A skin lesion imaged with a dermatoscope.
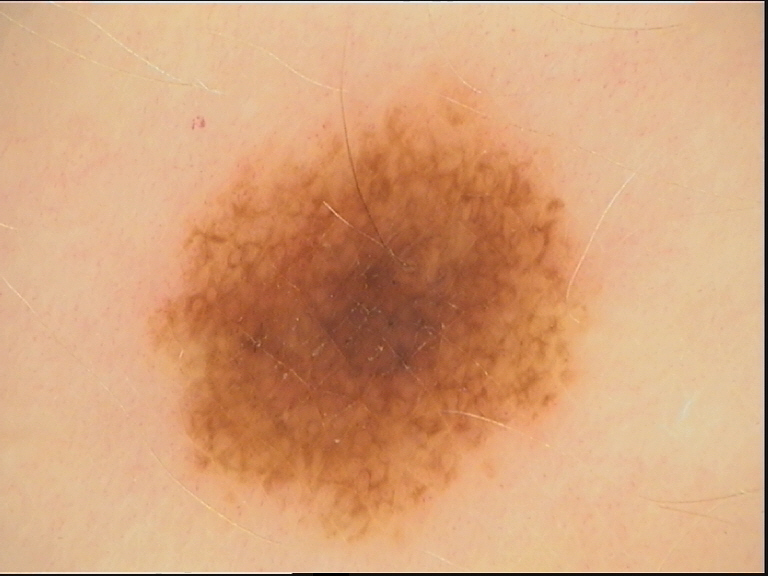{
  "diagnosis": {
    "name": "dysplastic junctional nevus",
    "code": "jd",
    "malignancy": "benign",
    "super_class": "melanocytic",
    "confirmation": "expert consensus"
  }
}